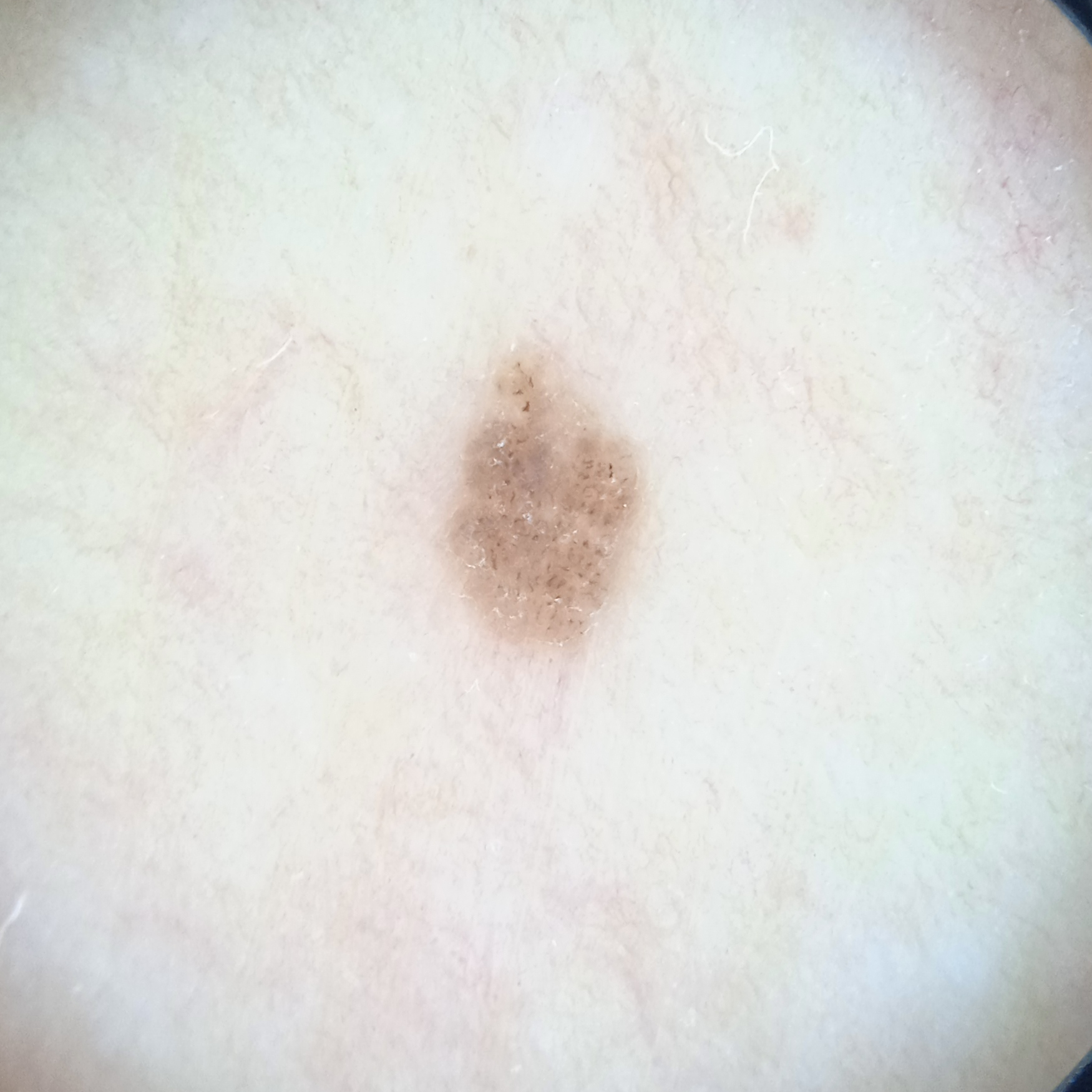A female patient age 60. By self-report, a personal history of skin cancer and a personal history of cancer. The patient says their skin tans without first burning. Acquired for a research image collection, with no referral diagnosis. A dermoscopy image of a skin lesion. Few moles overall by the patient's own estimate. The lesion is located on the torso. Measuring roughly 3.4 mm. The consensus diagnosis for this lesion was a melanocytic nevus.